Dermoscopy of a skin lesion.
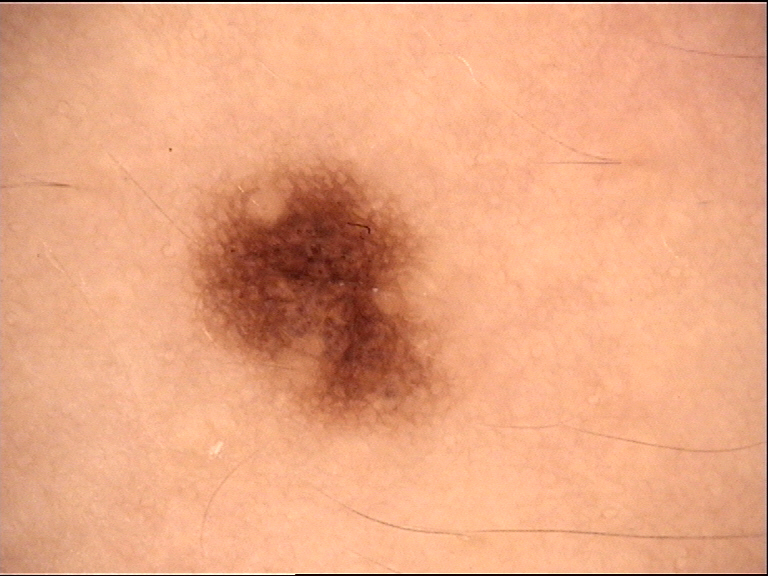diagnosis:
  name: dysplastic junctional nevus
  code: jd
  malignancy: benign
  super_class: melanocytic
  confirmation: expert consensus